A dermoscopic image of a skin lesion: 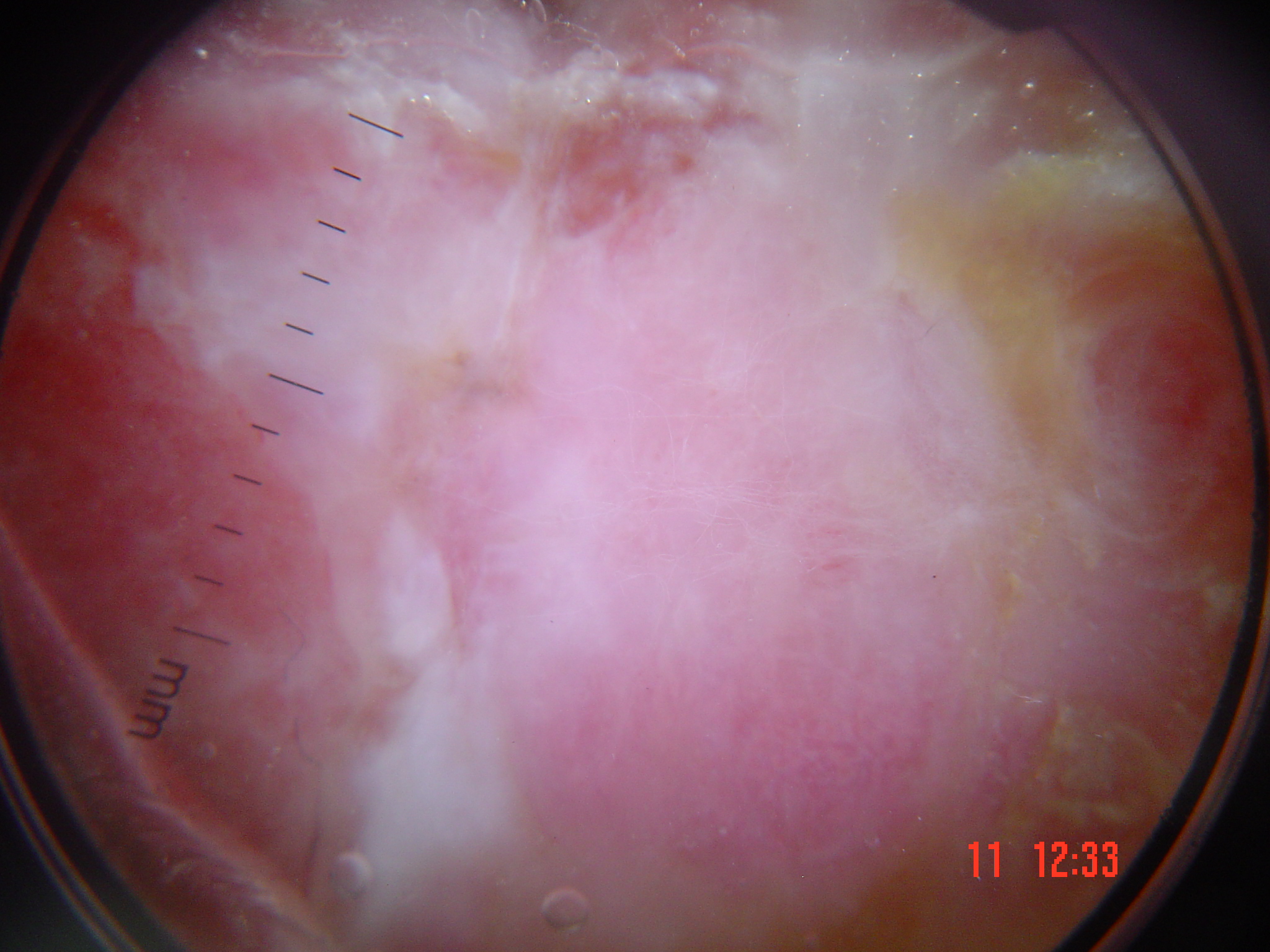Histopathology confirmed a malignancy — an acral nodular melanoma.